A dermoscopy image of a single skin lesion, a female subject approximately 15 years of age — 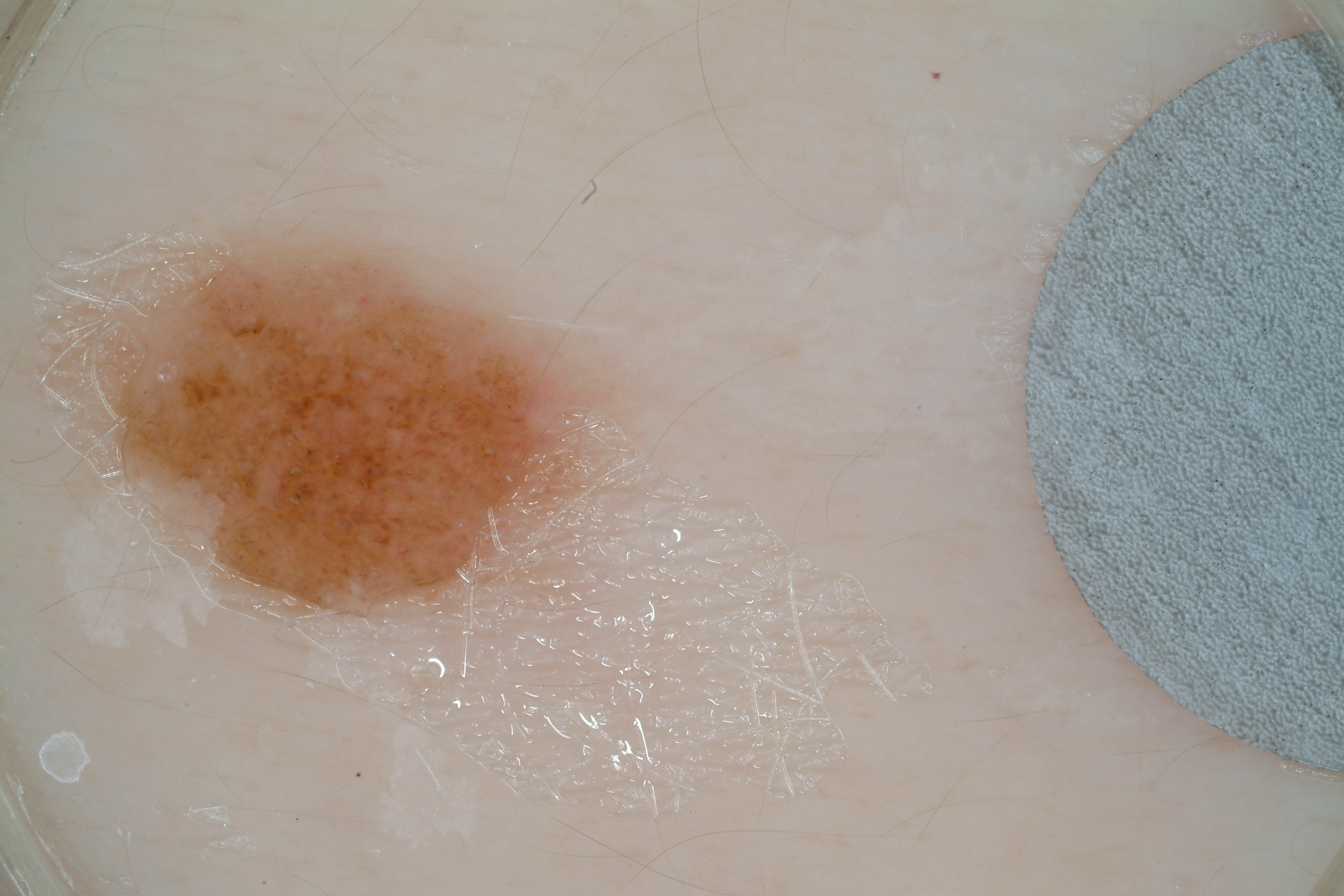The lesion spans left=121, top=255, right=545, bottom=622. Dermoscopic assessment notes no pigment network, globules, streaks, milia-like cysts, or negative network. The lesion occupies roughly 10% of the field. Expert review diagnosed this as a melanocytic nevus, a benign skin lesion.